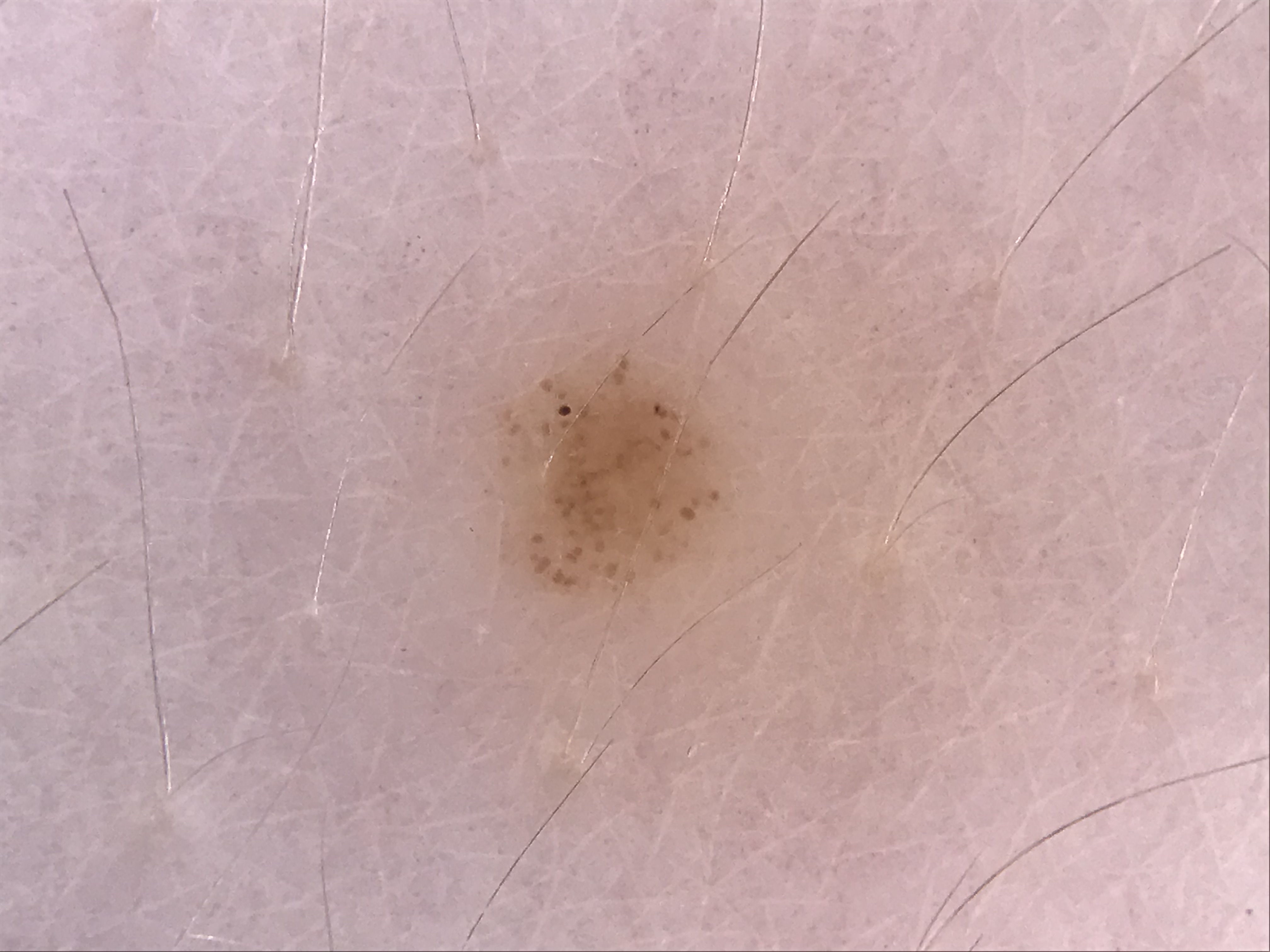Conclusion:
Labeled as a dysplastic junctional nevus.